A dermoscopic close-up of a skin lesion.
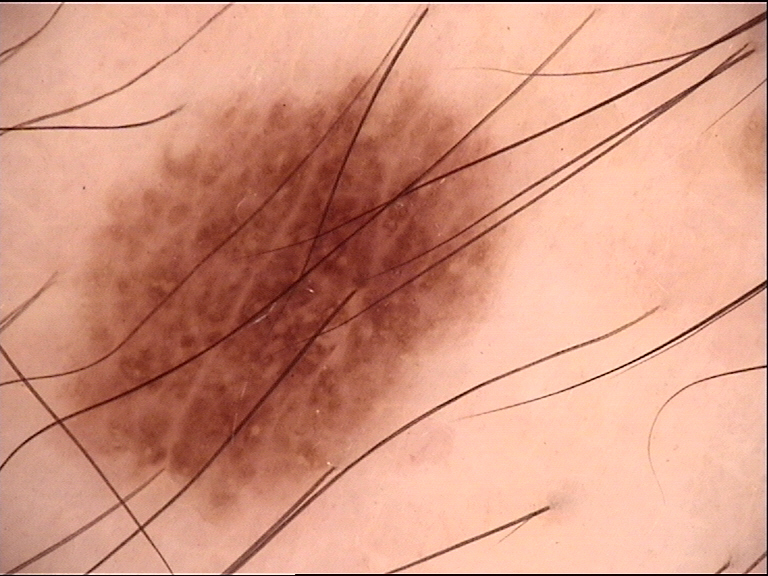Consistent with a benign lesion — a dysplastic junctional nevus.